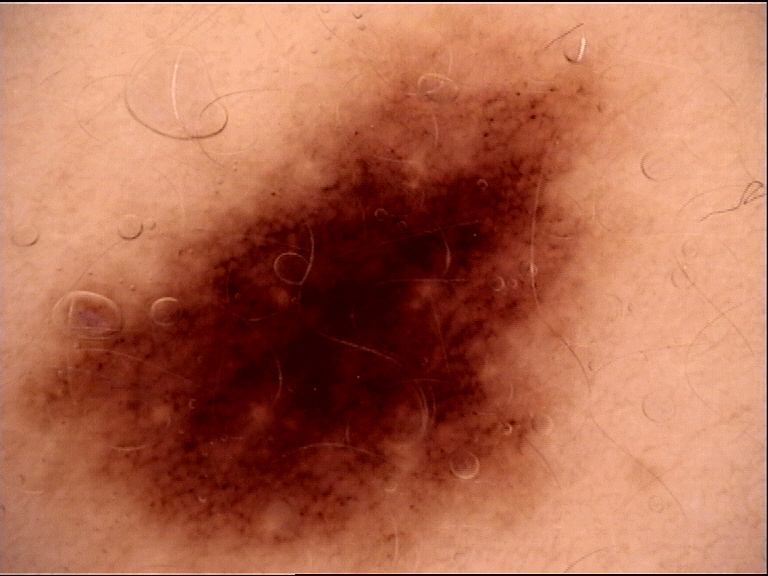A dermoscopic image of a skin lesion.
Classified as a dysplastic junctional nevus.